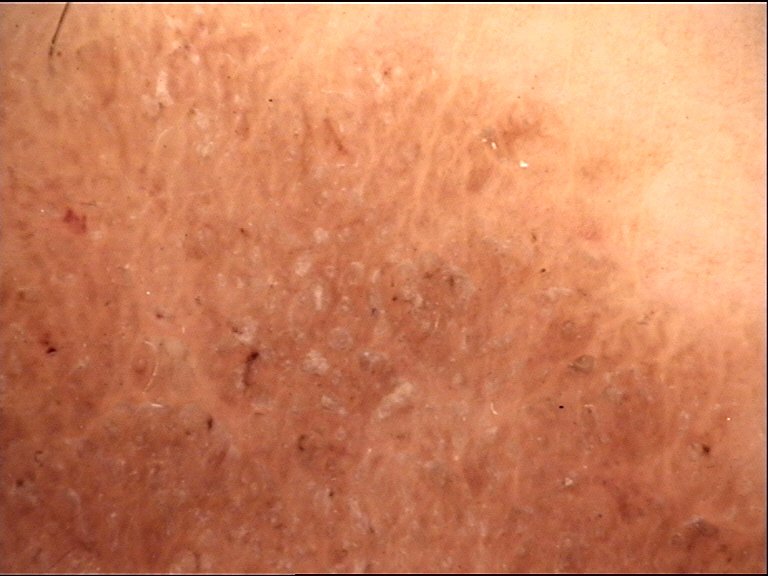{"diagnosis": {"name": "seborrheic keratosis", "code": "sk", "malignancy": "benign", "super_class": "non-melanocytic", "confirmation": "expert consensus"}}